The patient described the issue as a rash; associated systemic symptoms include fatigue; located on the back of the torso and front of the torso; symptoms reported: itching; the contributor is 18–29, female; present for one to four weeks; the lesion is described as rough or flaky and flat; this image was taken at an angle.
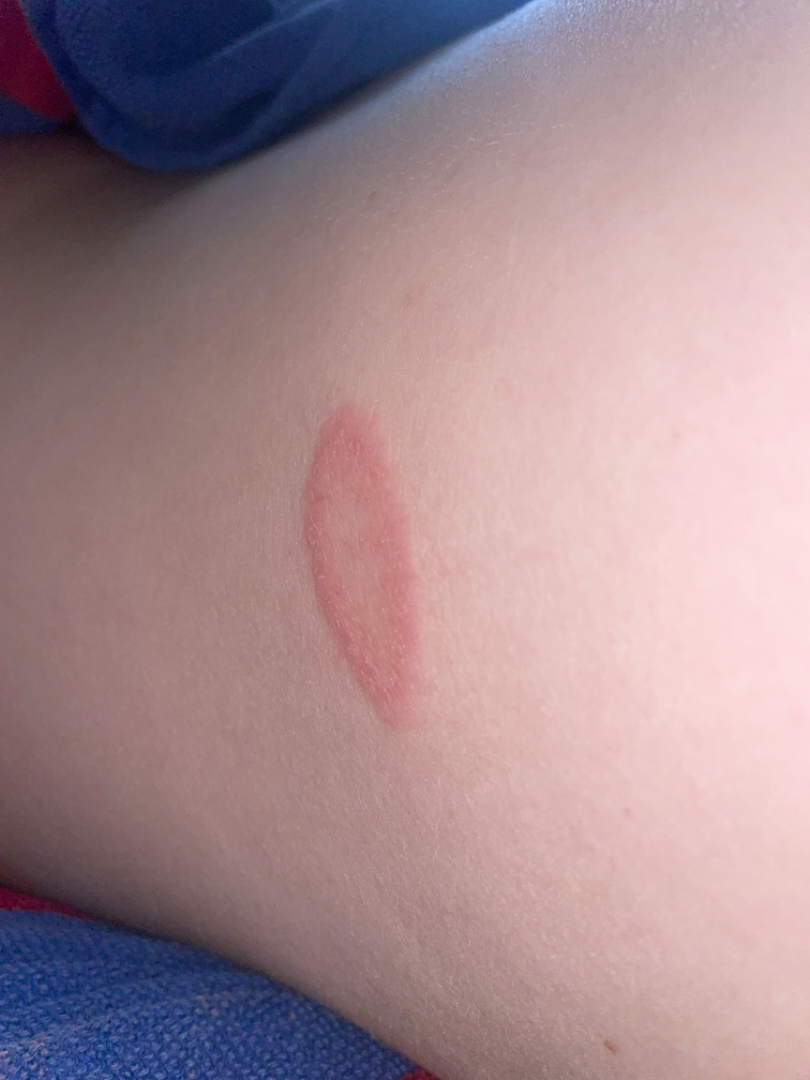<summary>
<differential>
  <leading>Pityriasis rosea</leading>
  <unlikely>Erythema annulare centrifugum, Tinea, Granuloma annulare</unlikely>
</differential>
</summary>